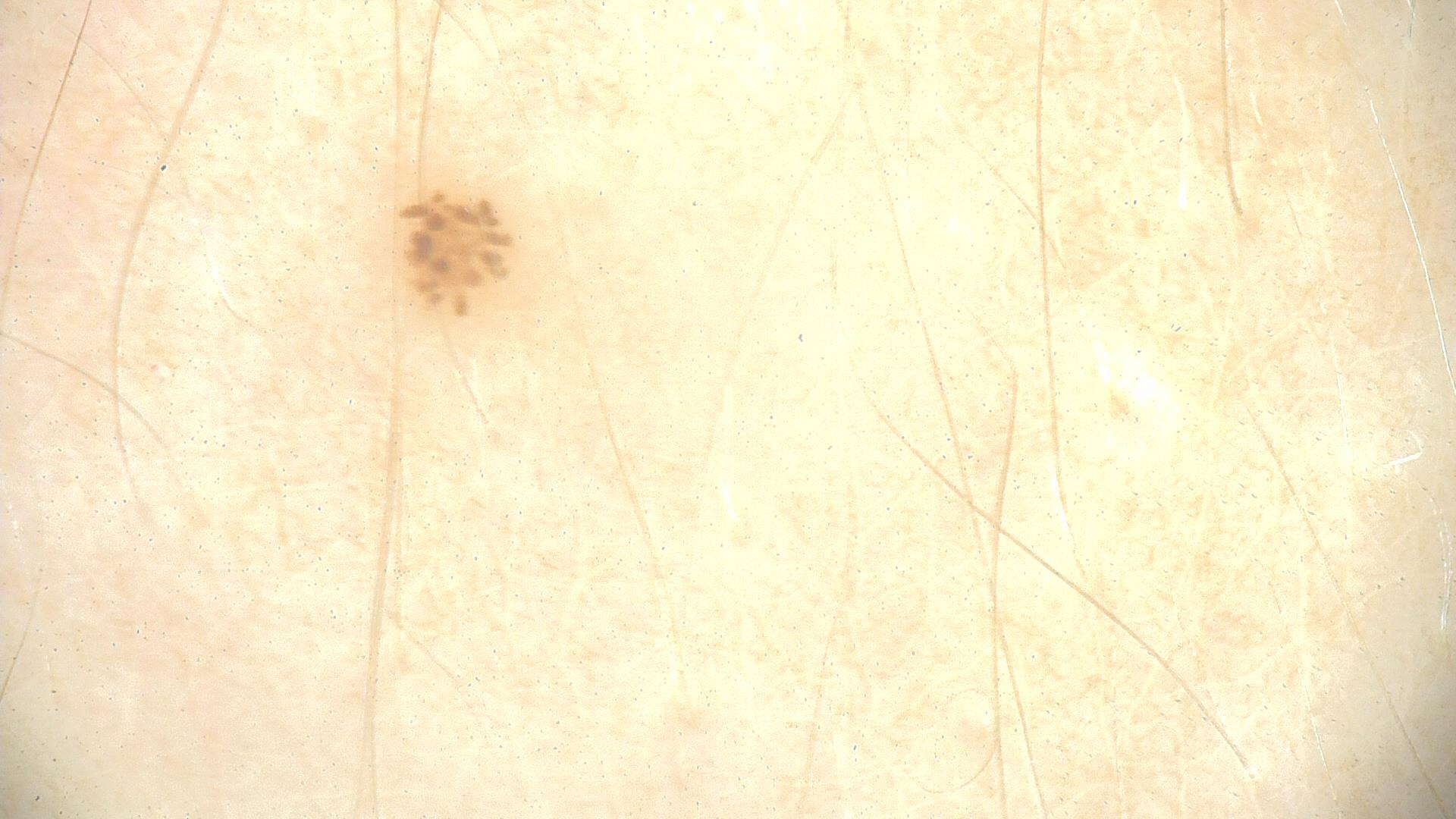Dermoscopy of a skin lesion. Consistent with a dysplastic junctional nevus.